A dermoscopic image of a skin lesion:
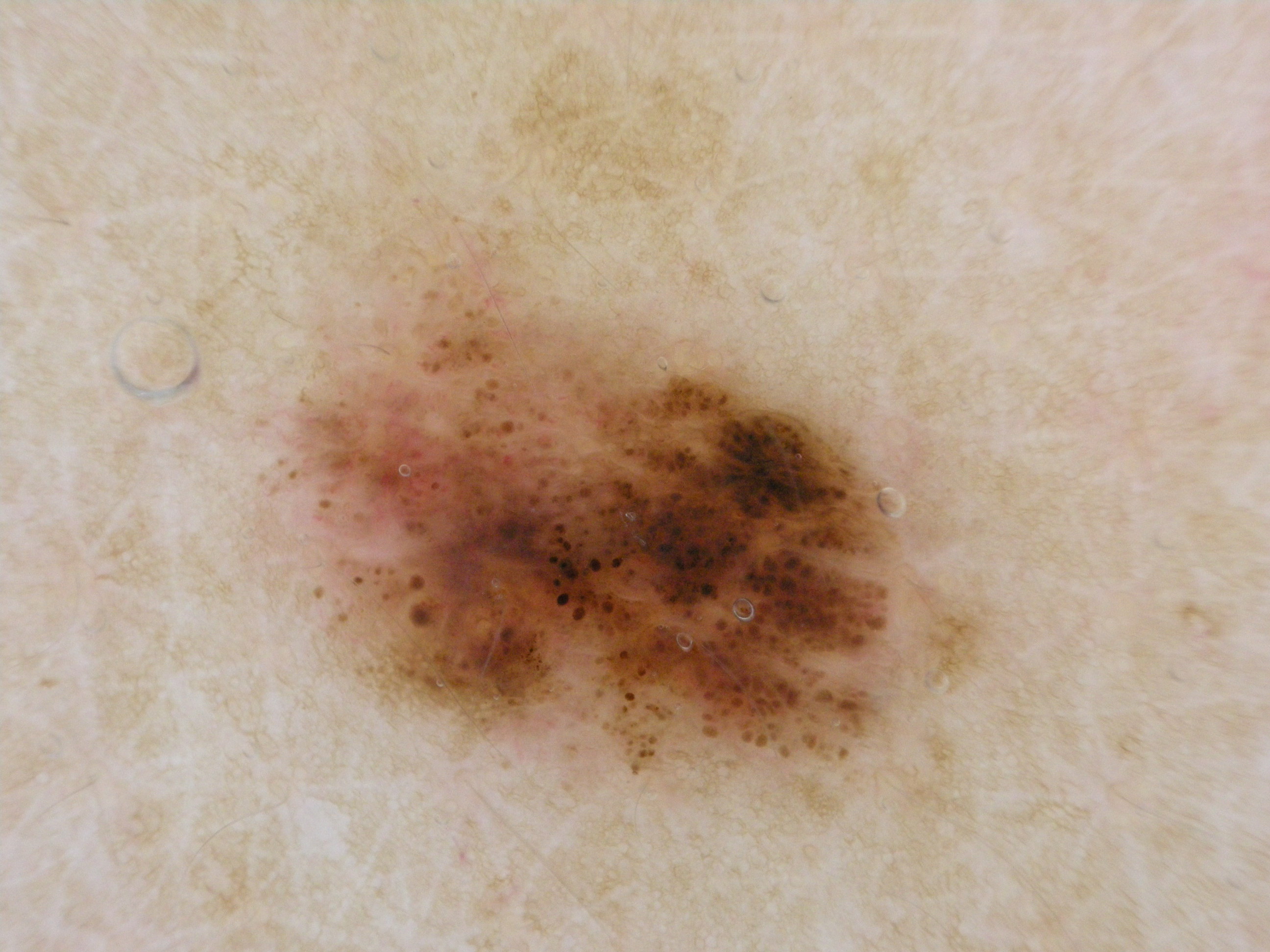dermoscopic_features:
  present:
    - pigment network
    - globules
  absent:
    - streaks
    - negative network
    - milia-like cysts
lesion_extent:
  approx_field_fraction_pct: 28
lesion_location:
  bbox_xyxy:
    - 239
    - 259
    - 1028
    - 817
diagnosis:
  name: melanoma
  malignancy: malignant
  lineage: melanocytic
  provenance: histopathology